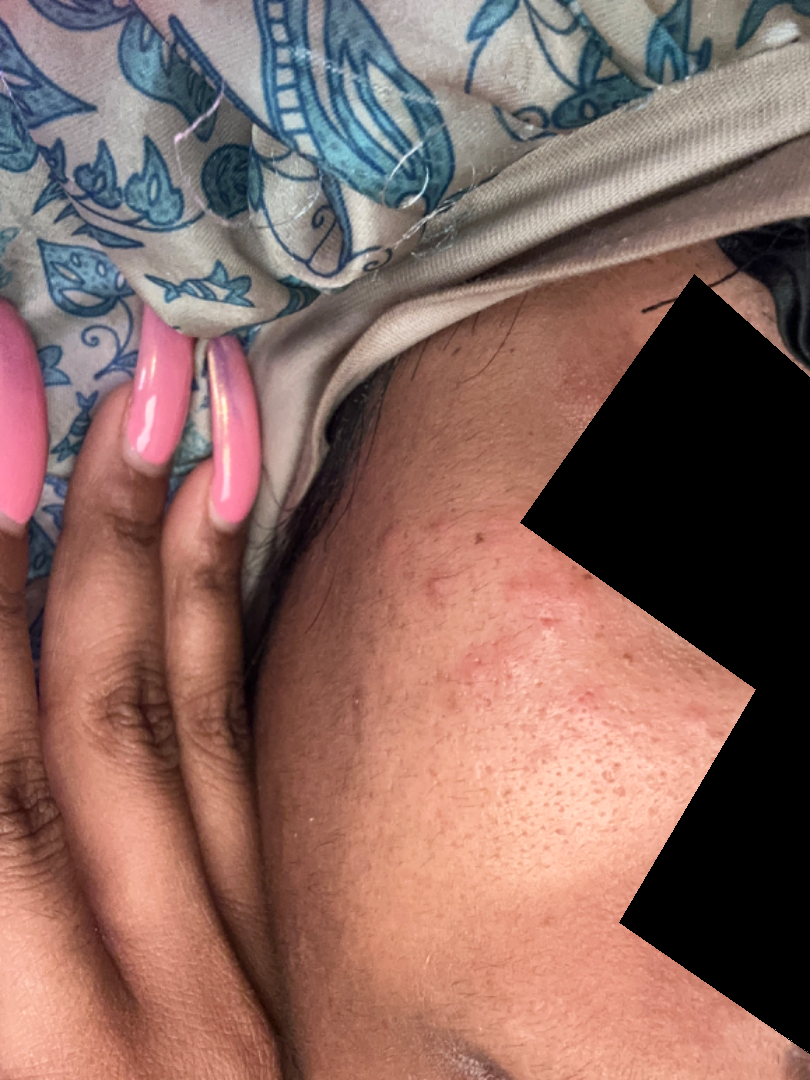patient's own categorization=a rash; patient-reported symptoms=none reported; onset=about one day; contributor=female, age 18–29; framing=at an angle; clinical impression=Acne and Rosacea were each considered, in no particular order.